By history, pesticide exposure; a male subject aged 74; a clinical close-up photograph of a skin lesion; the patient is Fitzpatrick phototype II: 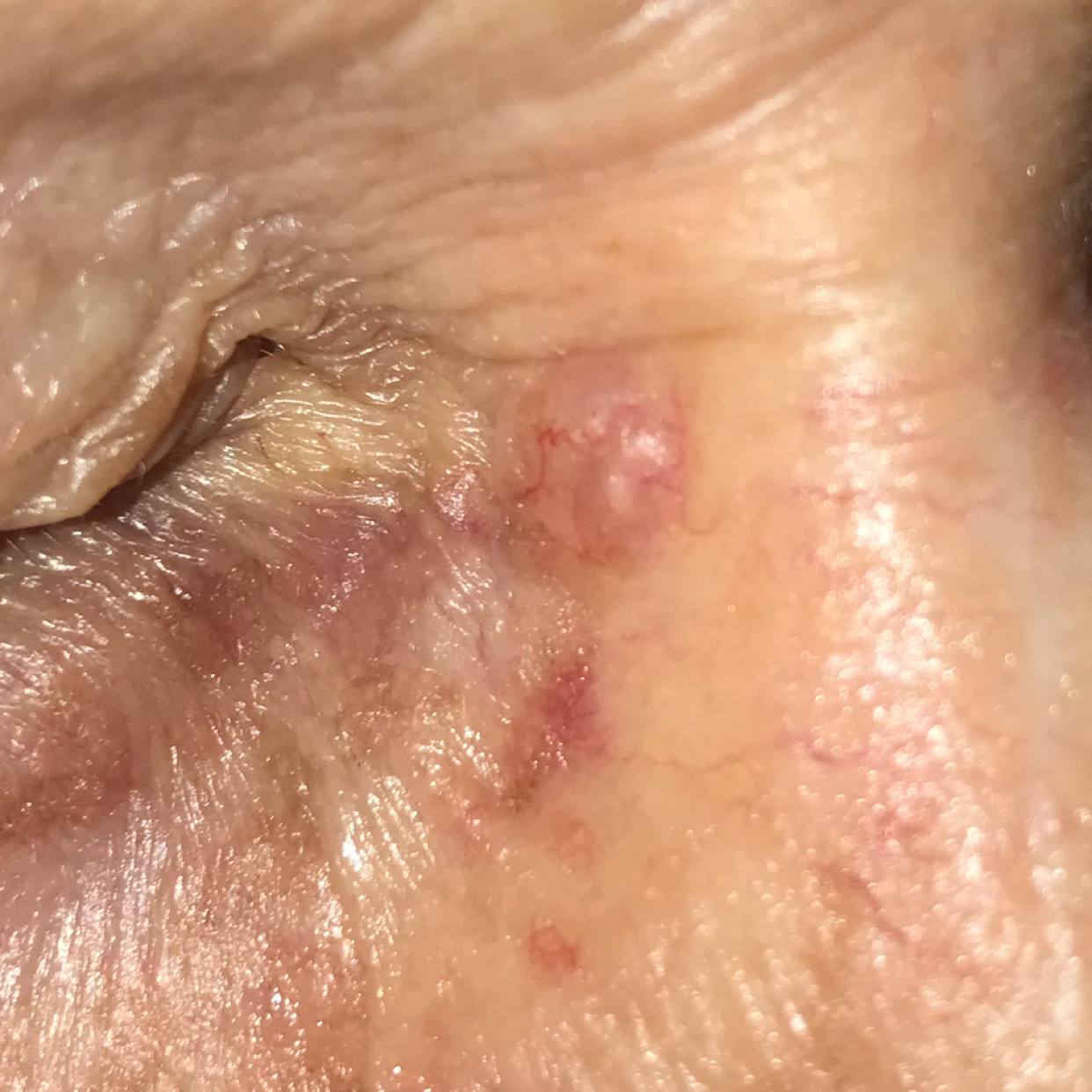| key | value |
|---|---|
| site | the face |
| pathology | basal cell carcinoma (biopsy-proven) |